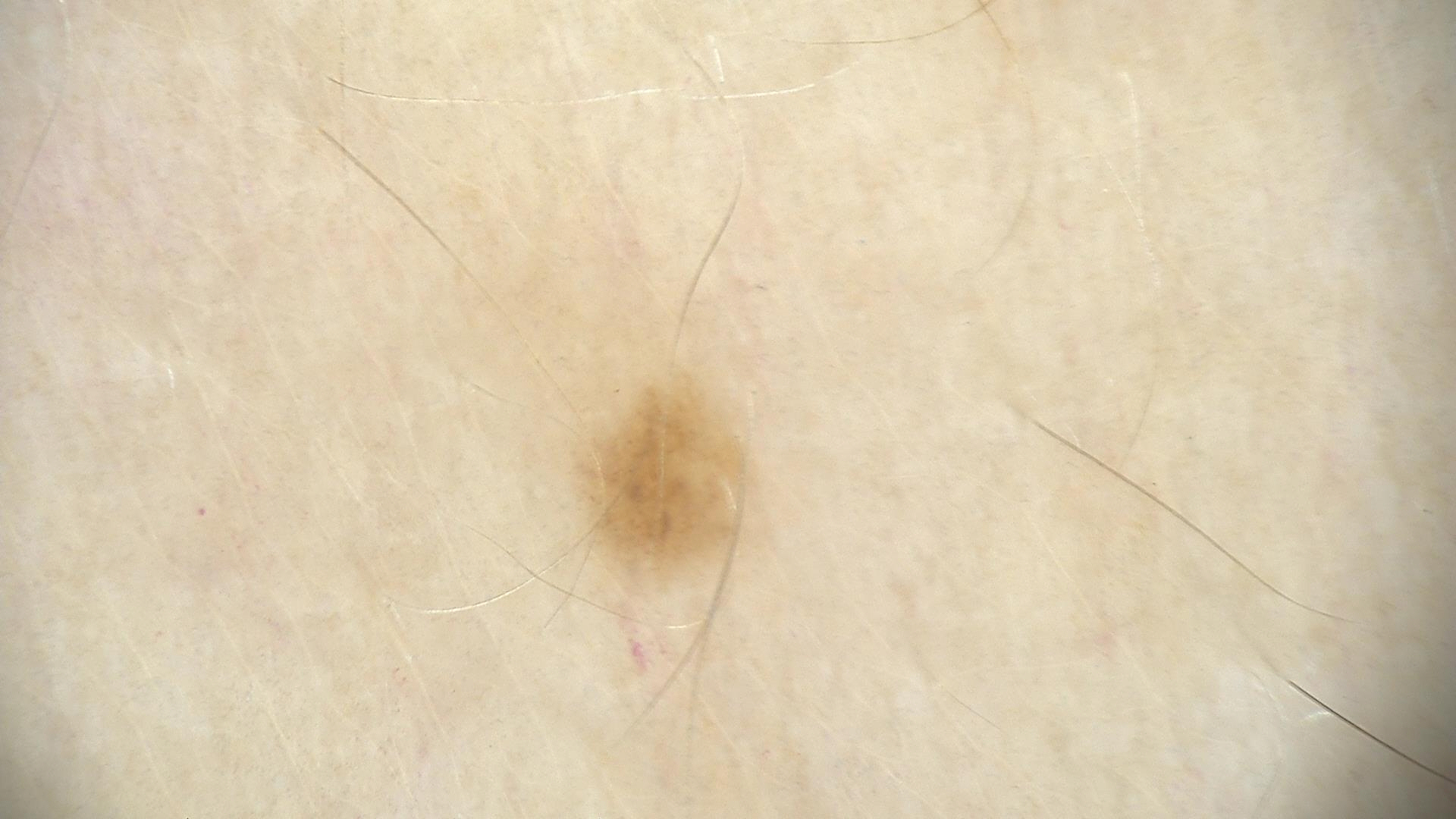Conclusion:
Labeled as a dysplastic junctional nevus.